Close-up view: 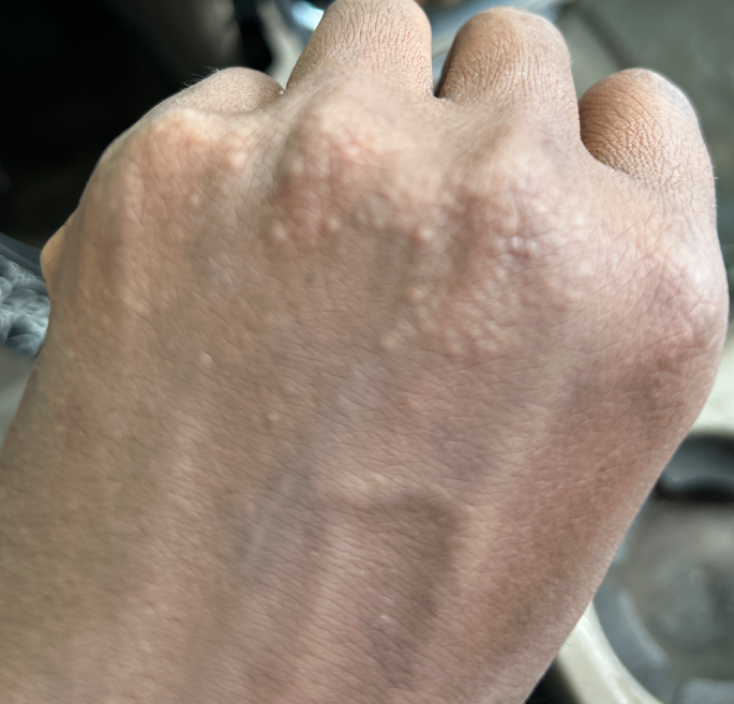assessment = not assessable.